A dermatoscopic image of a skin lesion: 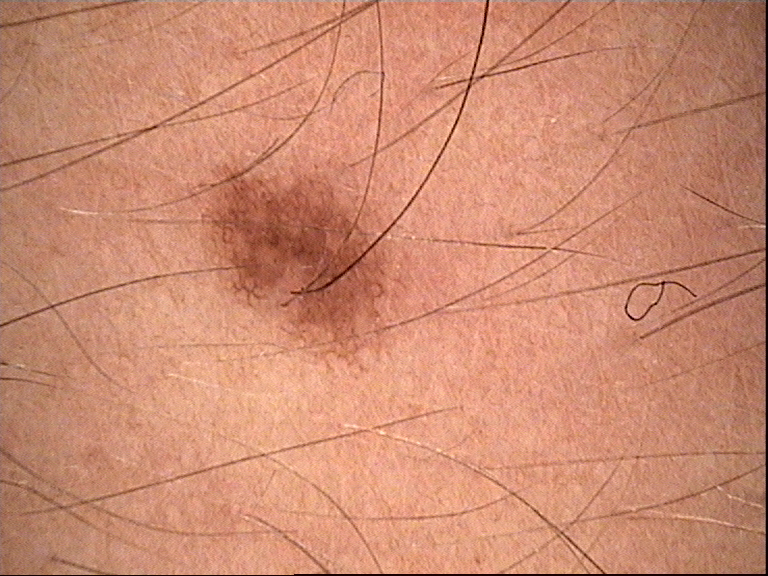Consistent with a dysplastic junctional nevus.